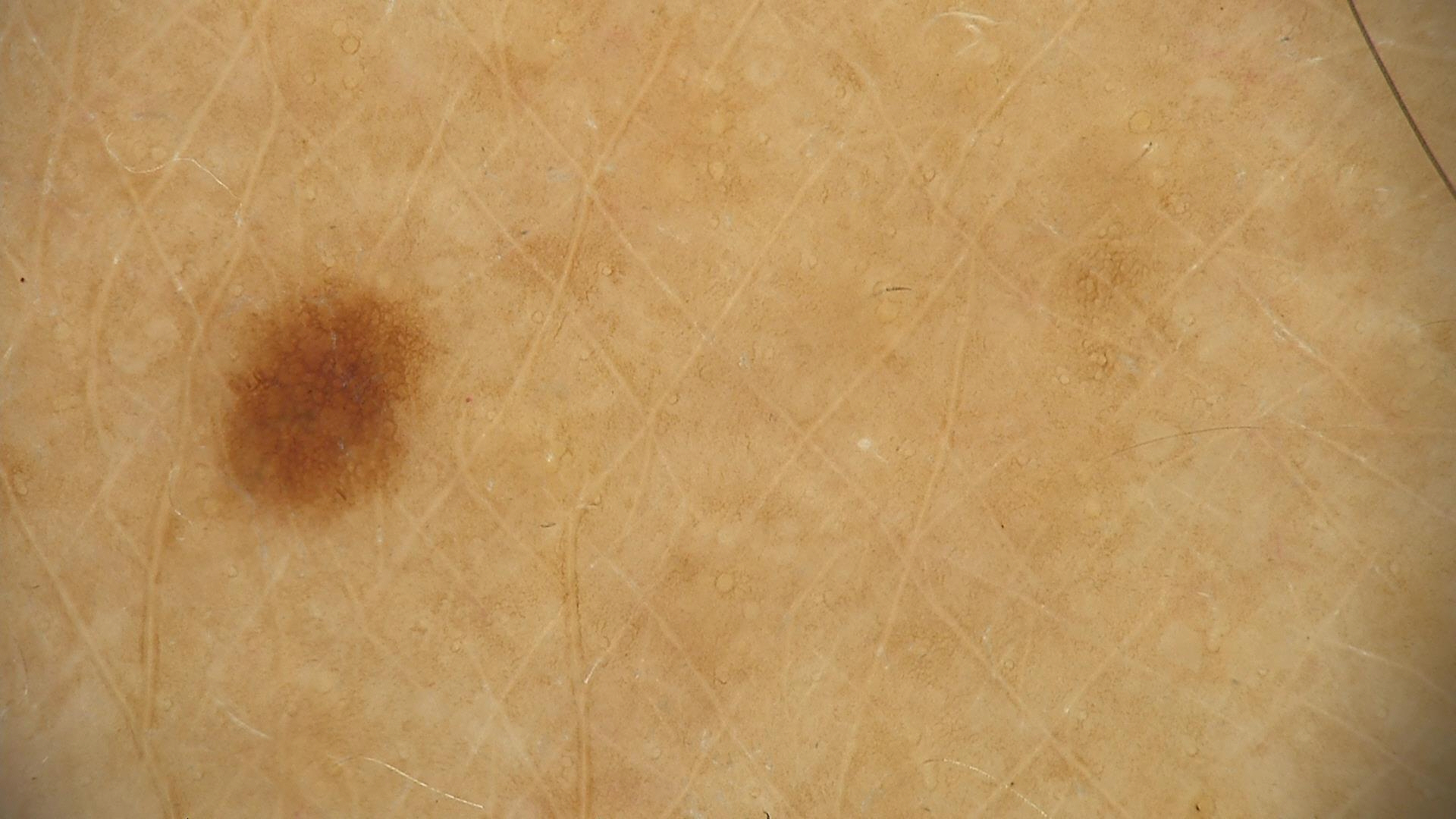A dermoscopic close-up of a skin lesion.
Diagnosed as a dysplastic junctional nevus.